A close-up photograph. The affected area is the front of the torso and back of the torso.
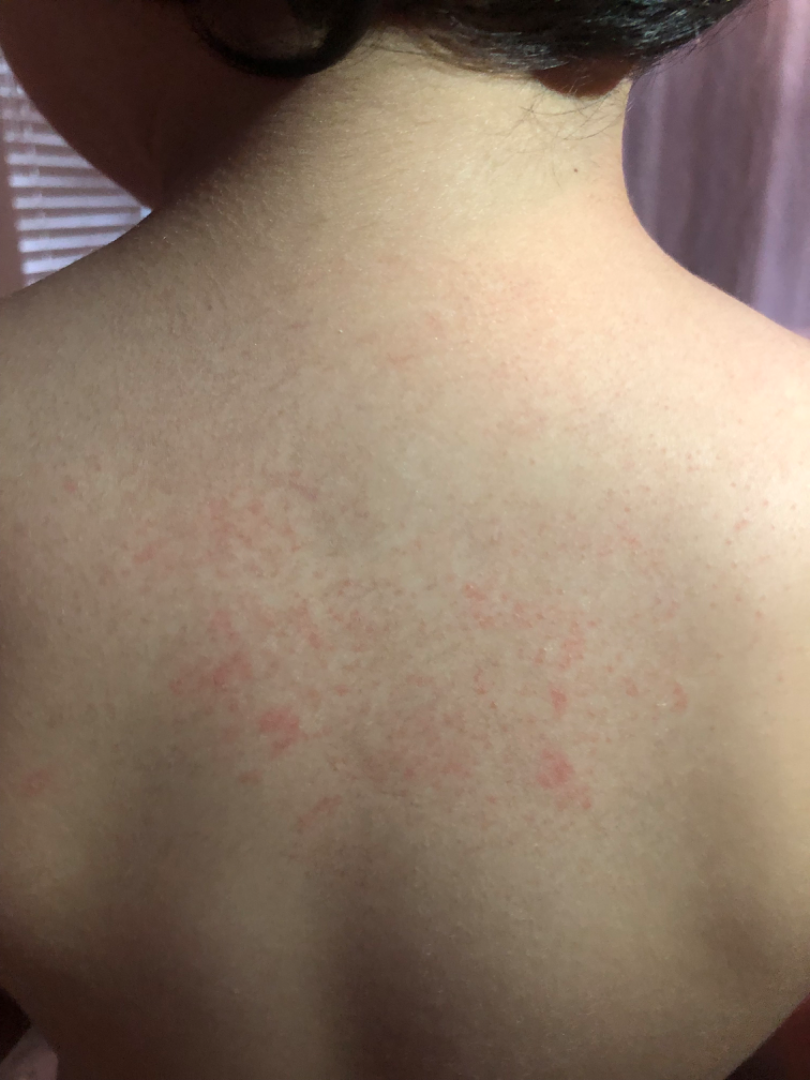skin tone — Fitzpatrick skin type III
symptoms — none reported
constitutional symptoms — fever
described texture — flat
differential diagnosis — Eczema (favored); Viral Exanthem (considered); Drug Rash (considered)